A close-up photograph. No relevant systemic symptoms. The condition has been present for about one day. Self-categorized by the patient as a rash. The patient is a female aged 18–29. The lesion is described as raised or bumpy. The affected area is the arm and leg. The lesion is associated with bothersome appearance, enlargement and itching: 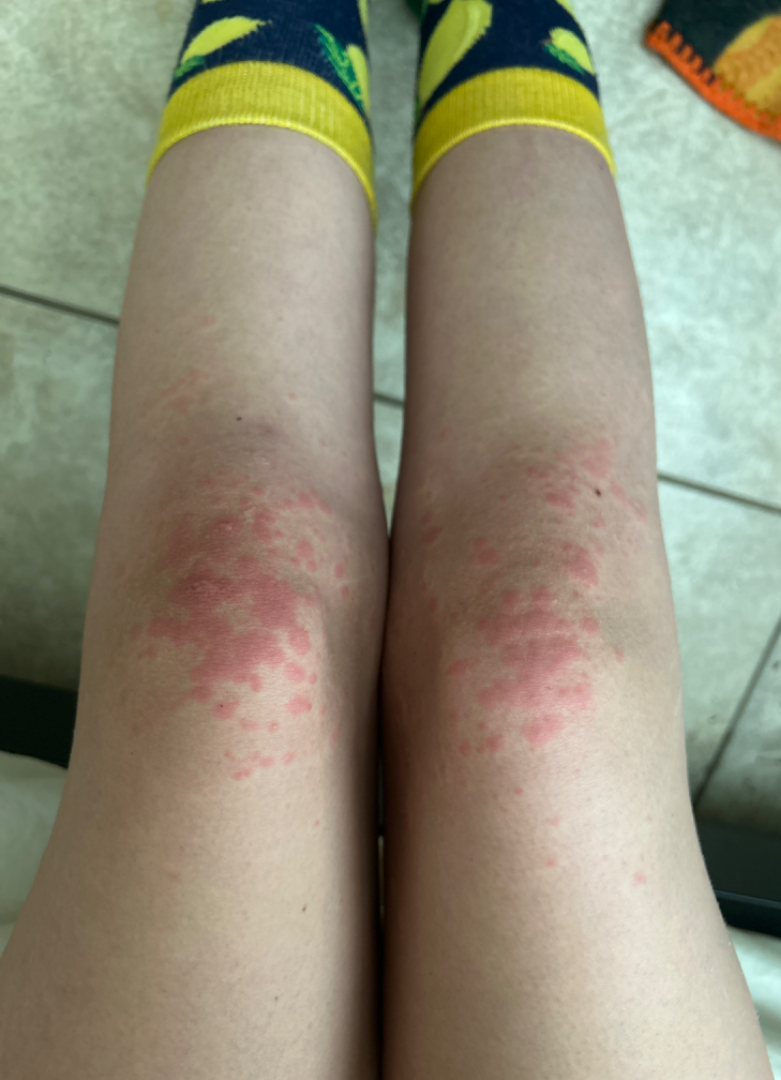Q: What is the differential diagnosis?
A: the reviewer's impression was Viral Exanthem